Close-up view; the affected area is the arm — 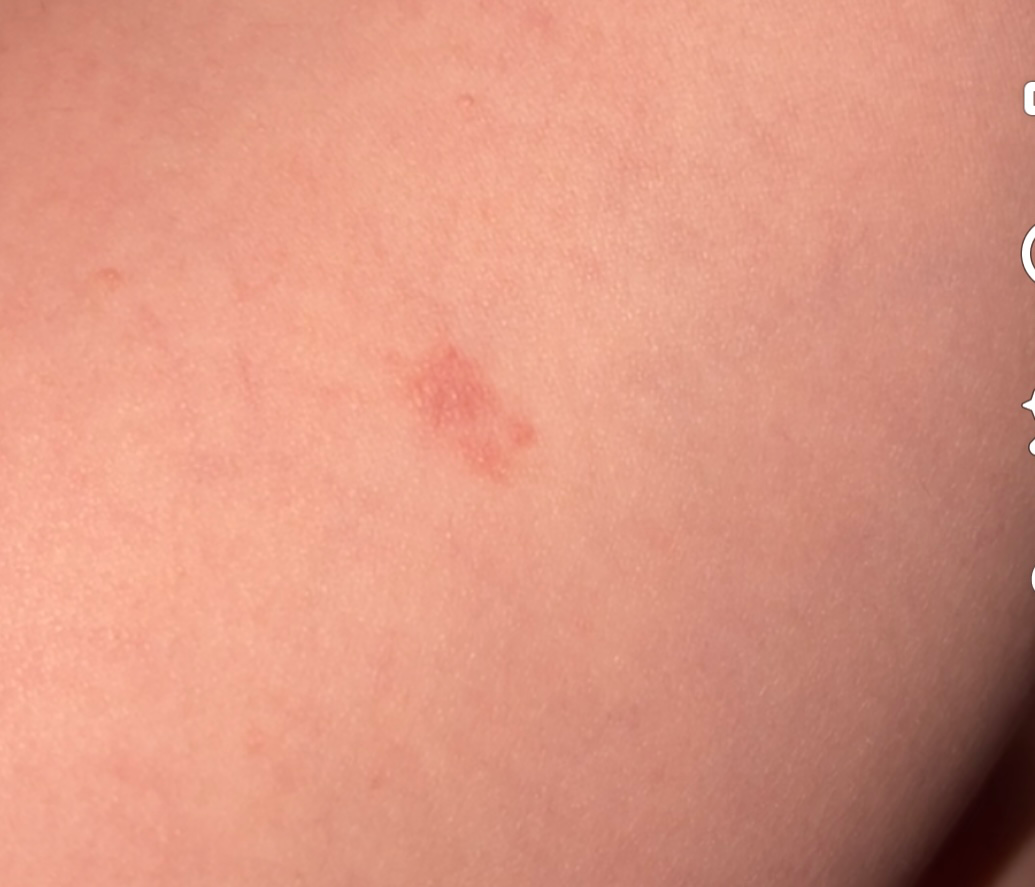Texture is reported as raised or bumpy. The contributor reports the condition has been present for about one day. On photographic review: consistent with Eczema.